A skin lesion imaged with a dermatoscope:
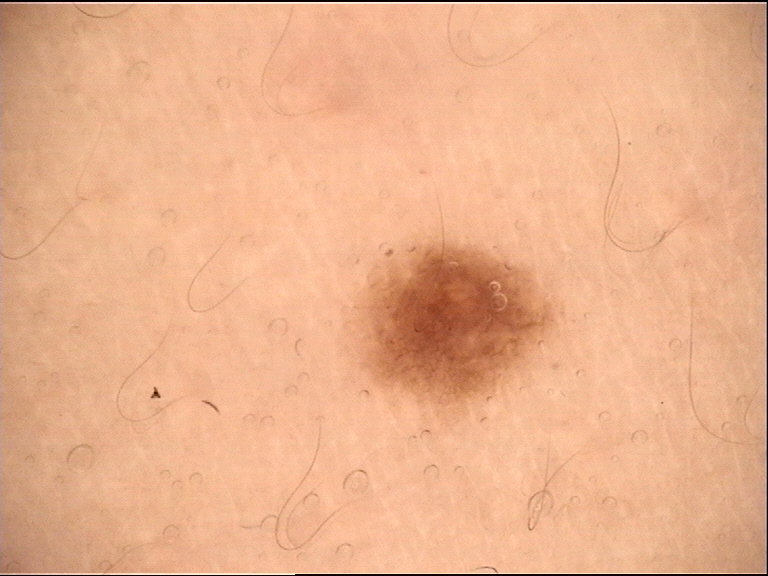{
  "diagnosis": {
    "name": "dysplastic junctional nevus",
    "code": "jd",
    "malignancy": "benign",
    "super_class": "melanocytic",
    "confirmation": "expert consensus"
  }
}